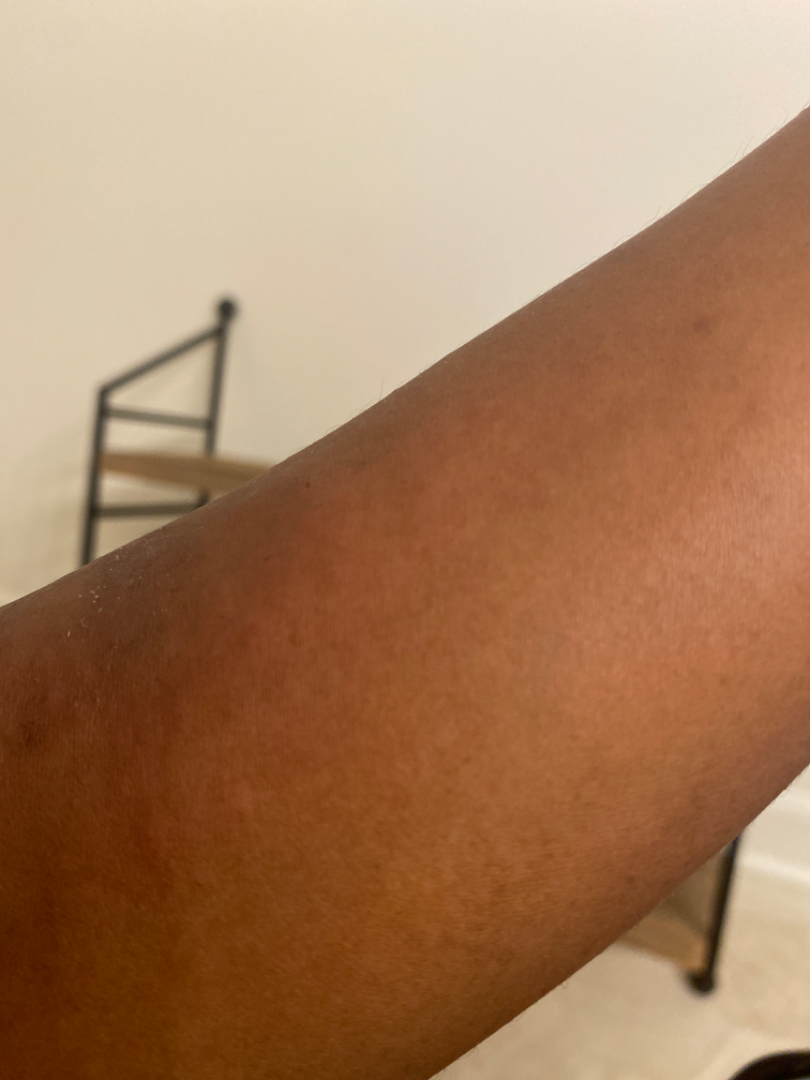subject: female, age 18–29
shot type: at an angle
site: arm
dermatologist impression: Eczema (most likely); Scabies (unlikely); Allergic Contact Dermatitis (unlikely); Tinea (unlikely); Psoriasis (unlikely)